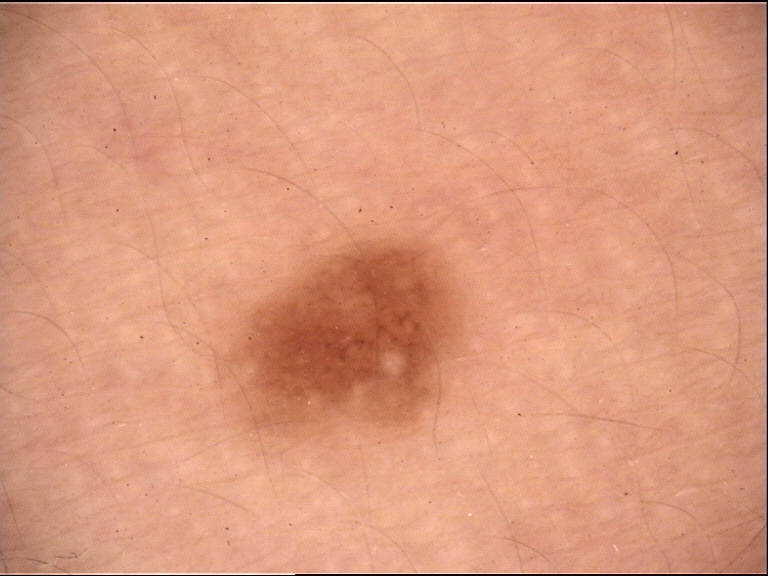The diagnostic label was a junctional nevus.